A dermatoscopic image of a skin lesion: 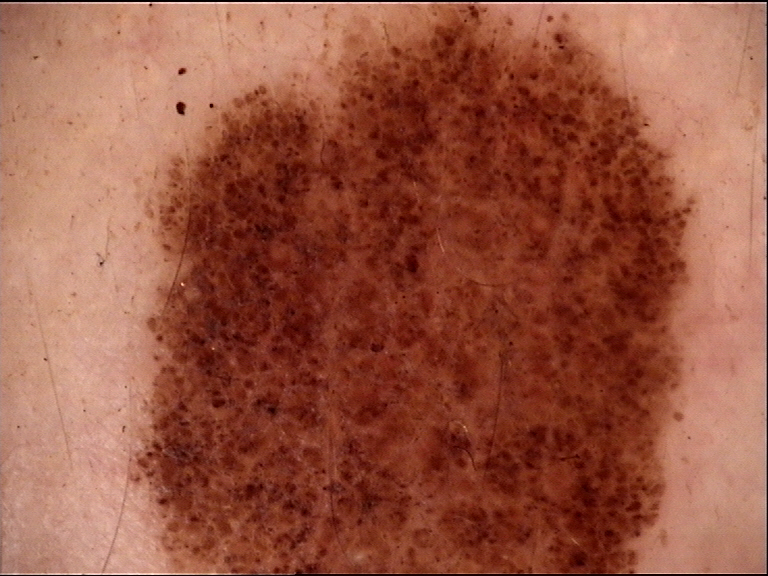assessment = dysplastic compound nevus (expert consensus)